The lesion involves the front of the torso; close-up view.
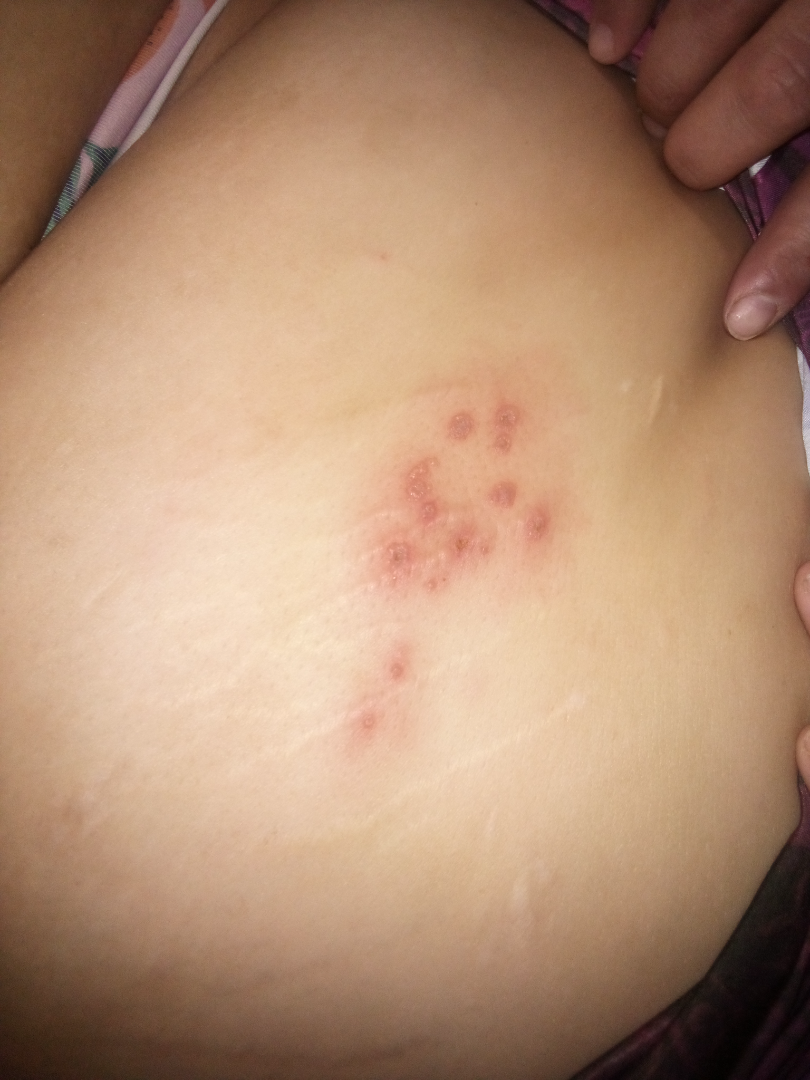No relevant systemic symptoms. The condition has been present for less than one week. Fitzpatrick phototype III; non-clinician graders estimated Monk Skin Tone 5 (US pool) or 3 (India pool). The contributor reports the lesion is raised or bumpy. The patient described the issue as skin that appeared healthy to them. A single dermatologist reviewed the case: most likely Herpes Simplex; an alternative is Molluscum Contagiosum; also consider Allergic Contact Dermatitis.